A dermatoscopic image of a skin lesion: 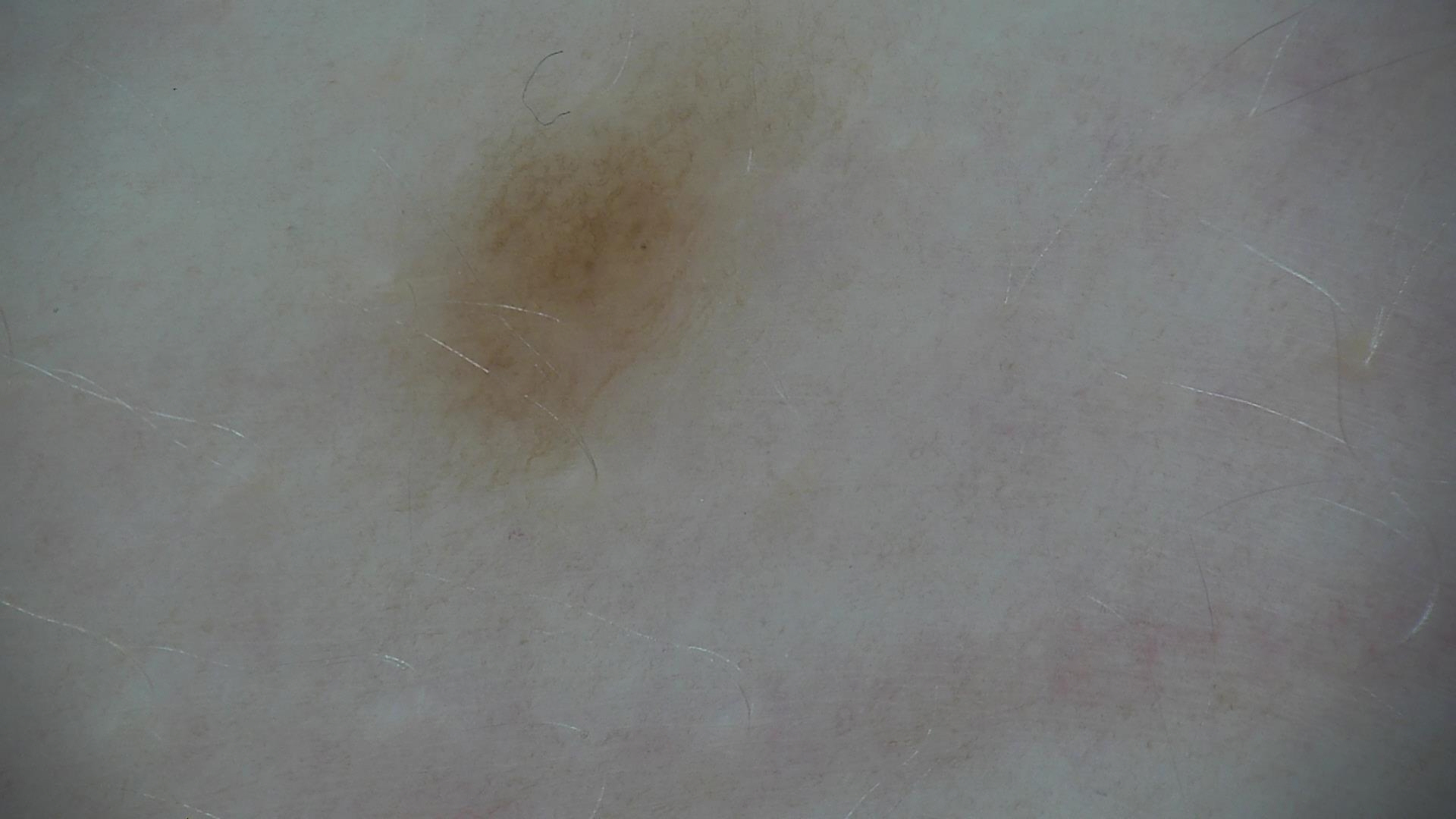category = banal
label = junctional nevus (expert consensus)